Reported lesion symptoms include itching, reported duration is about one day, located on the leg, a close-up photograph, the patient notes the lesion is raised or bumpy, FST III; lay reviewers estimated Monk Skin Tone 2 or 3:
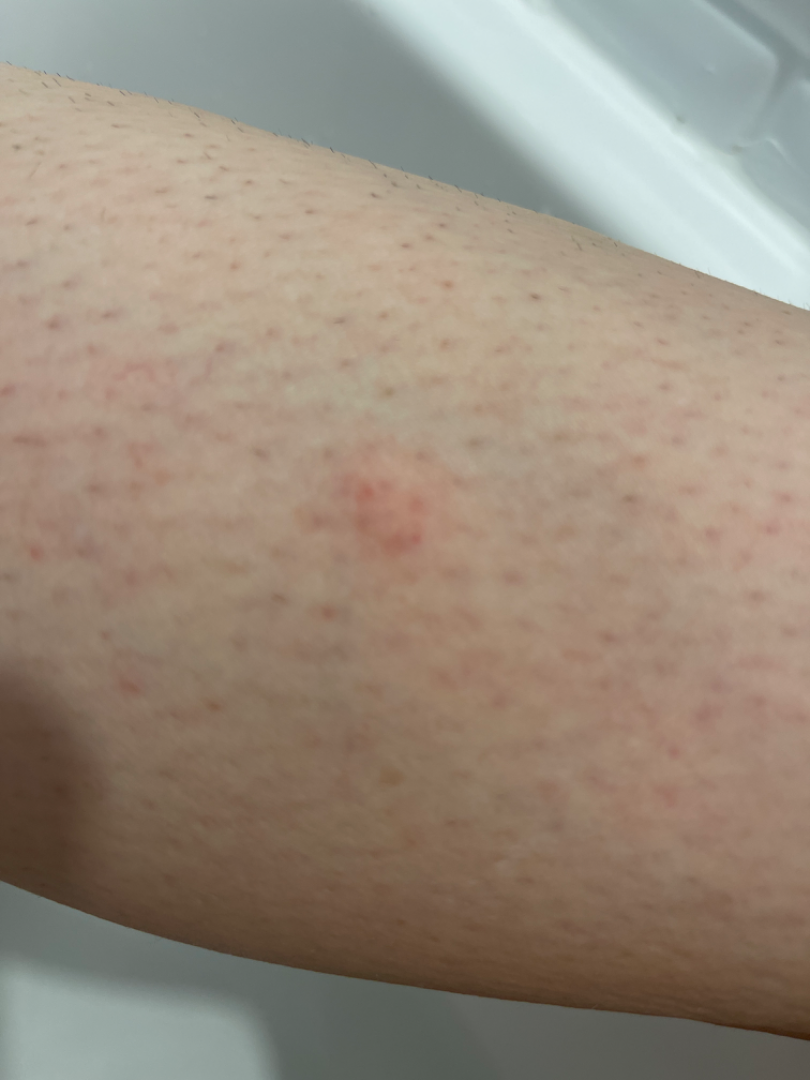The skin condition could not be confidently assessed from this image.